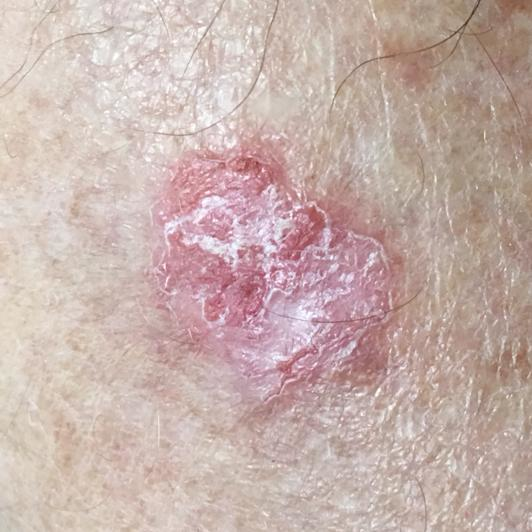Pathology: Biopsy-confirmed as a squamous cell carcinoma.